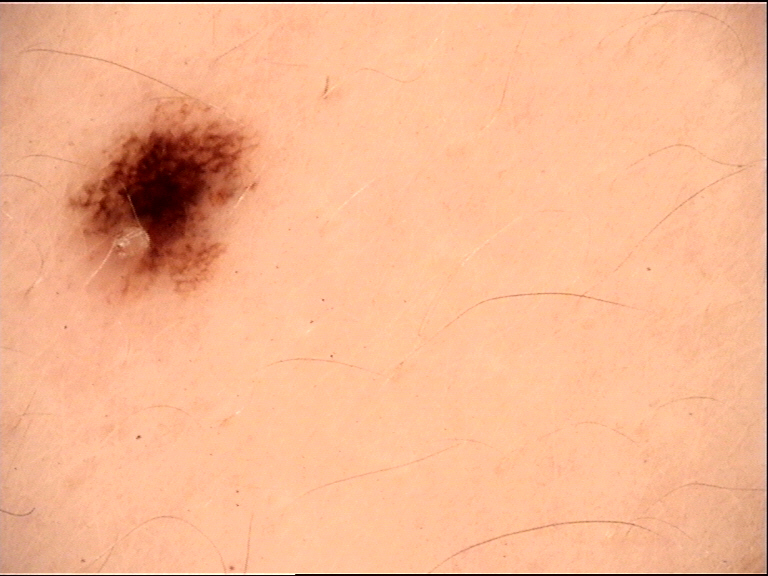Case:
• modality: dermoscopy
• category: banal
• diagnosis: junctional nevus (expert consensus)